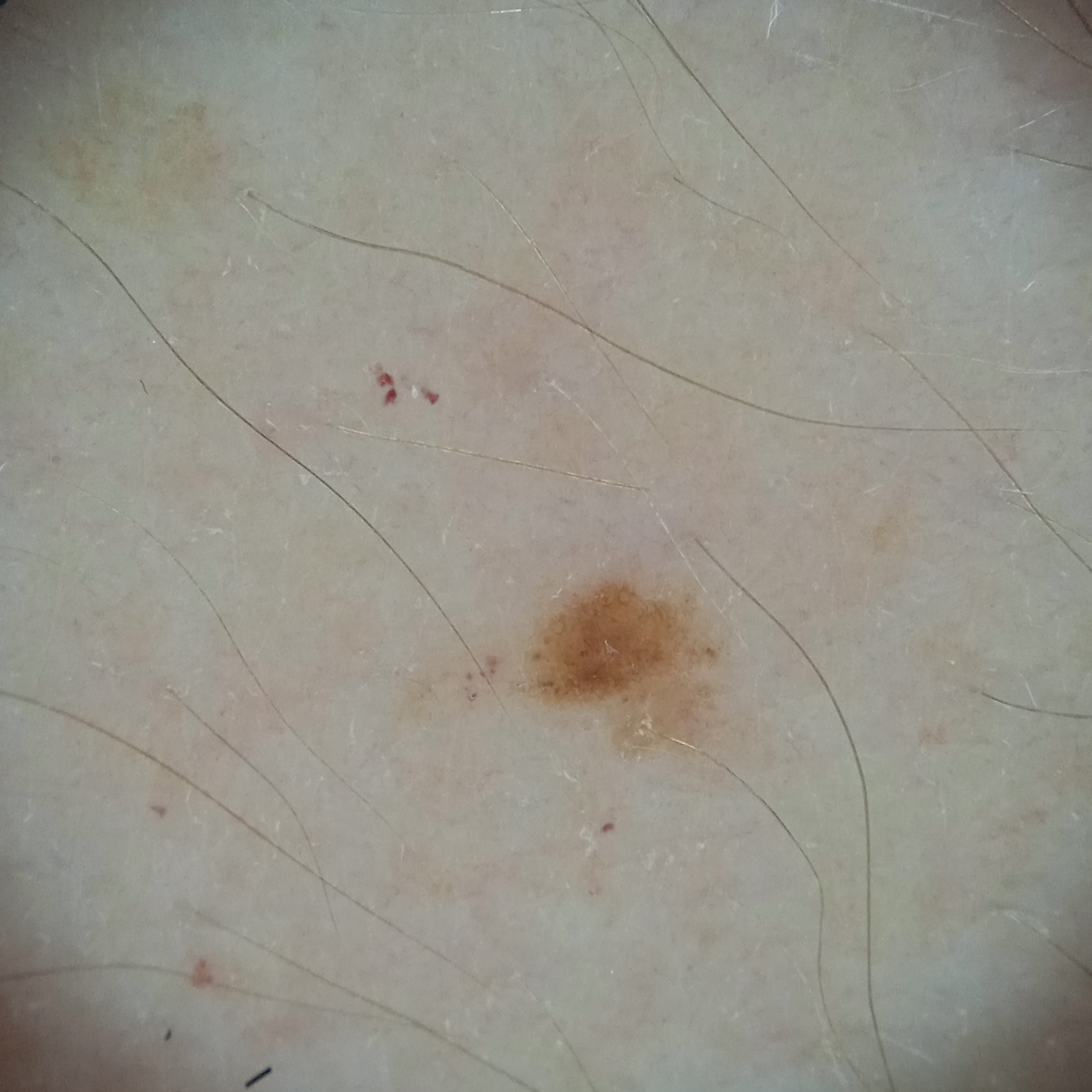  image: dermoscopic image
  patient:
    age: 35
    sex: female
  lesion_location: an arm
  diagnosis:
    name: melanocytic nevus
    malignancy: benign